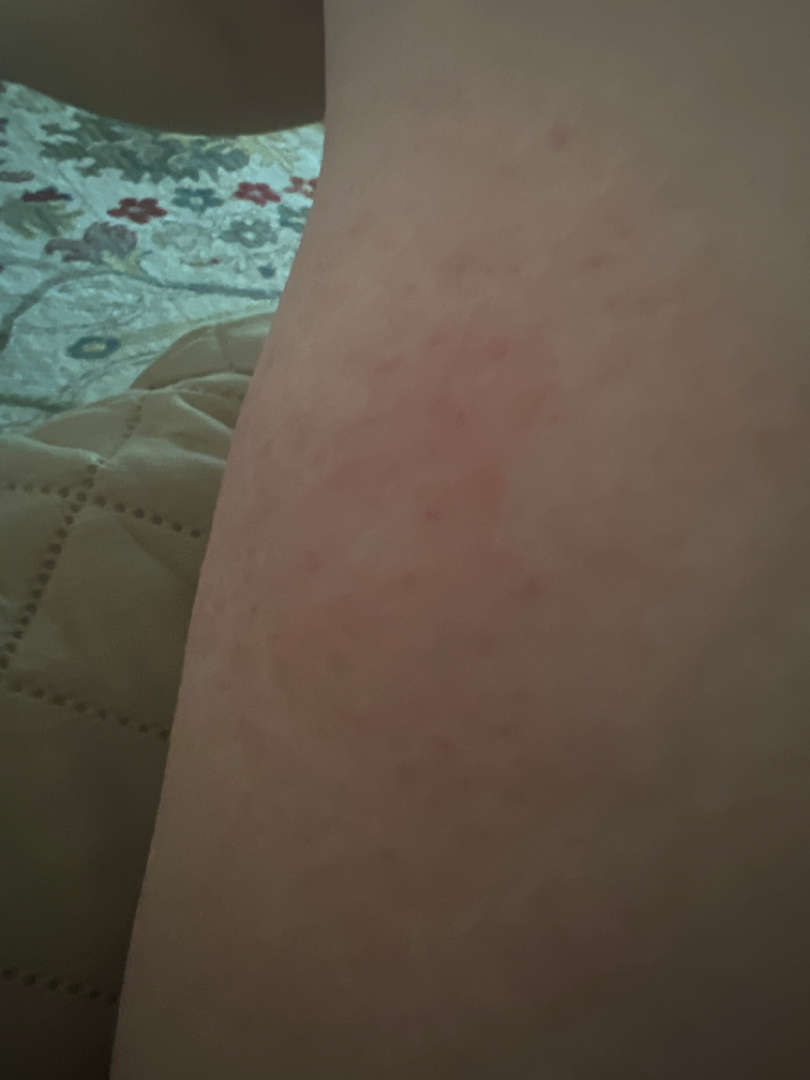Background: The subject is 70–79, female. The patient considered this a rash. Reported duration is less than one week. Skin tone: Fitzpatrick III. Located on the leg. Symptoms reported: itching. The photograph is a close-up of the affected area. The lesion is described as raised or bumpy. The patient reported no systemic symptoms. Findings: Three dermatologists each reviewed the case: the leading impression is Eczema; possibly Allergic Contact Dermatitis.